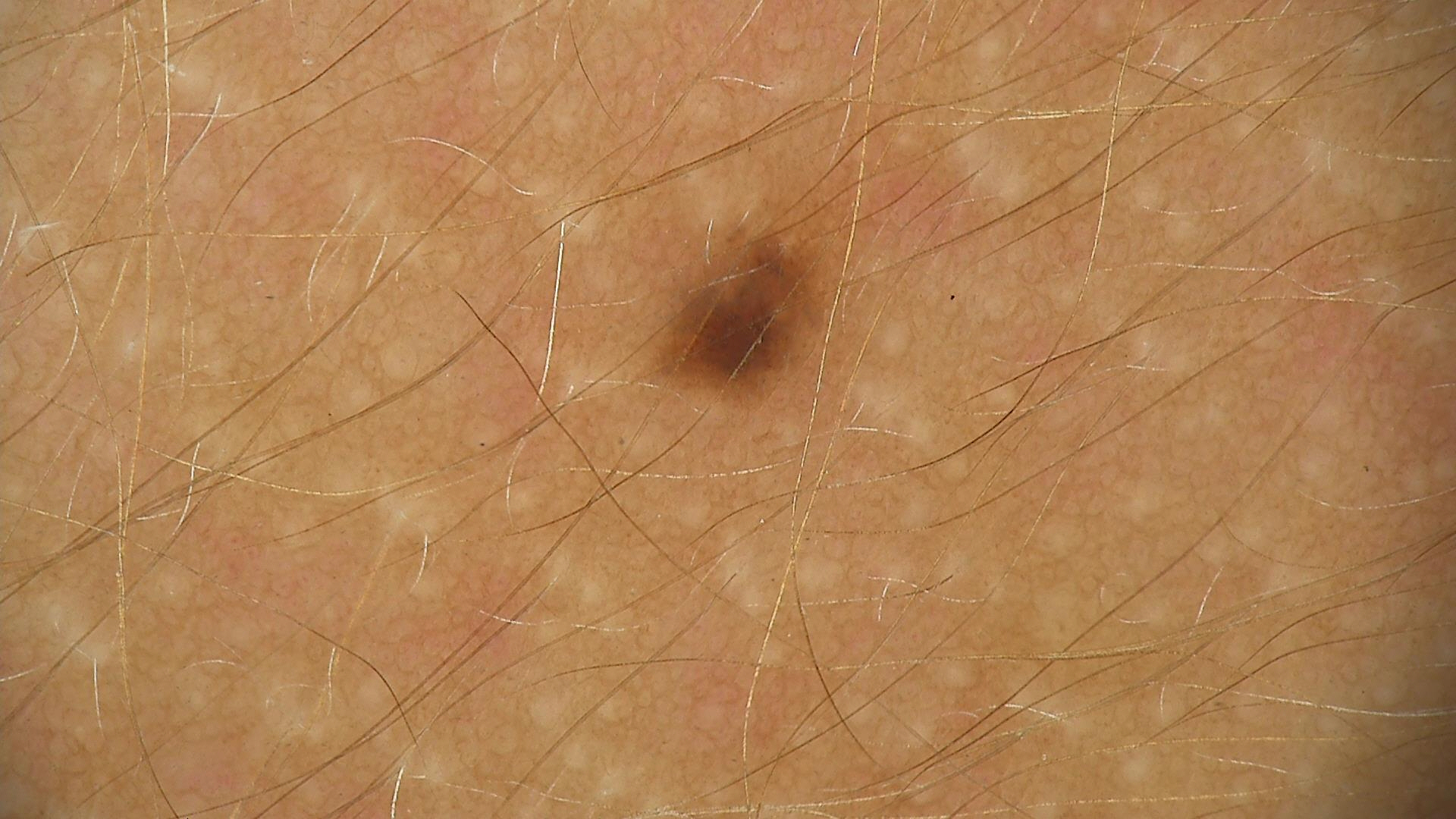imaging: dermoscopy, diagnosis: dysplastic junctional nevus (expert consensus).